A dermoscopic image of a skin lesion.
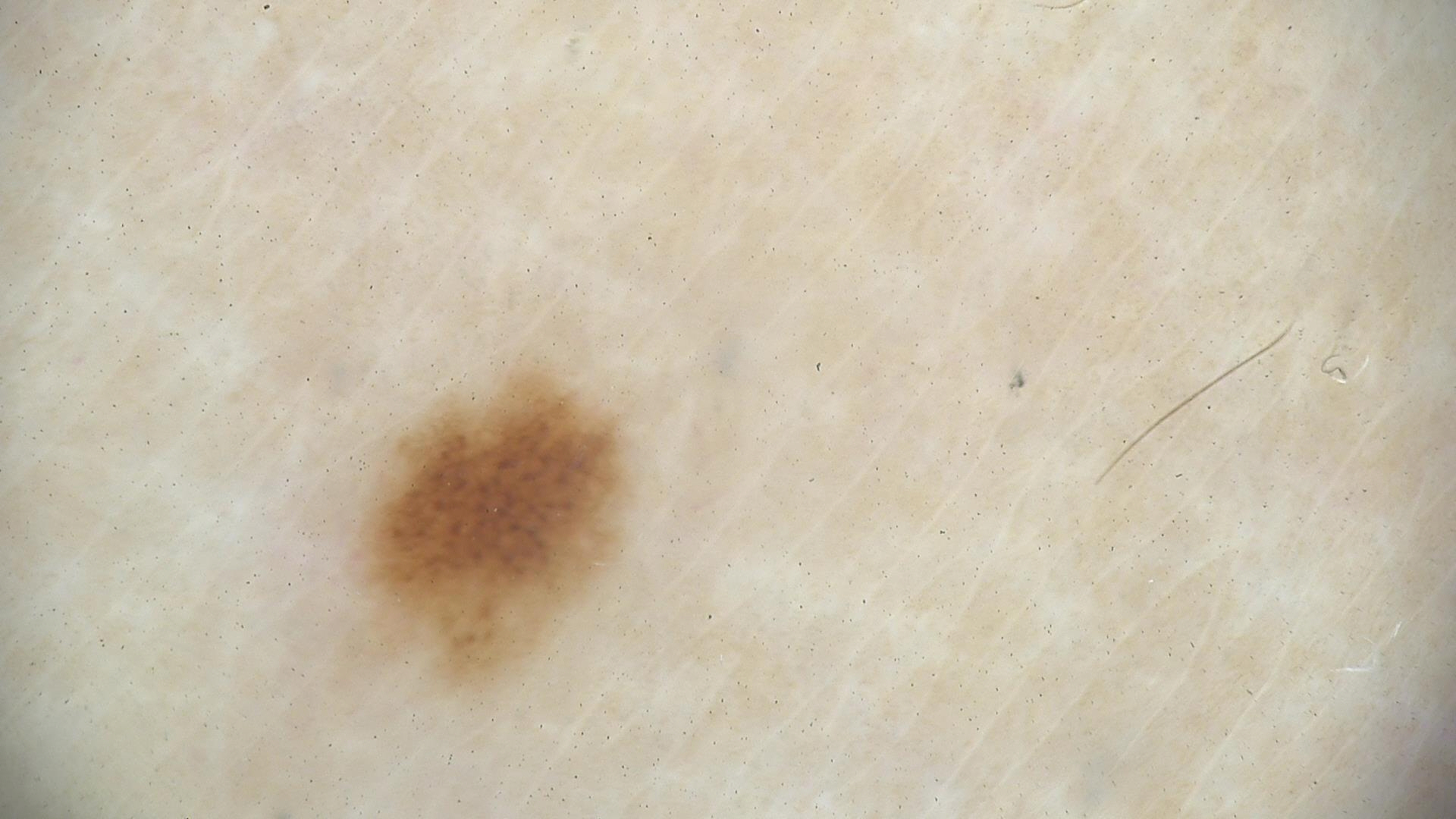class = dysplastic junctional nevus (expert consensus).